The patient says their skin reddens with sun exposure; imaged for a research study, with no referral diagnosis recorded; the patient describes having few moles overall:
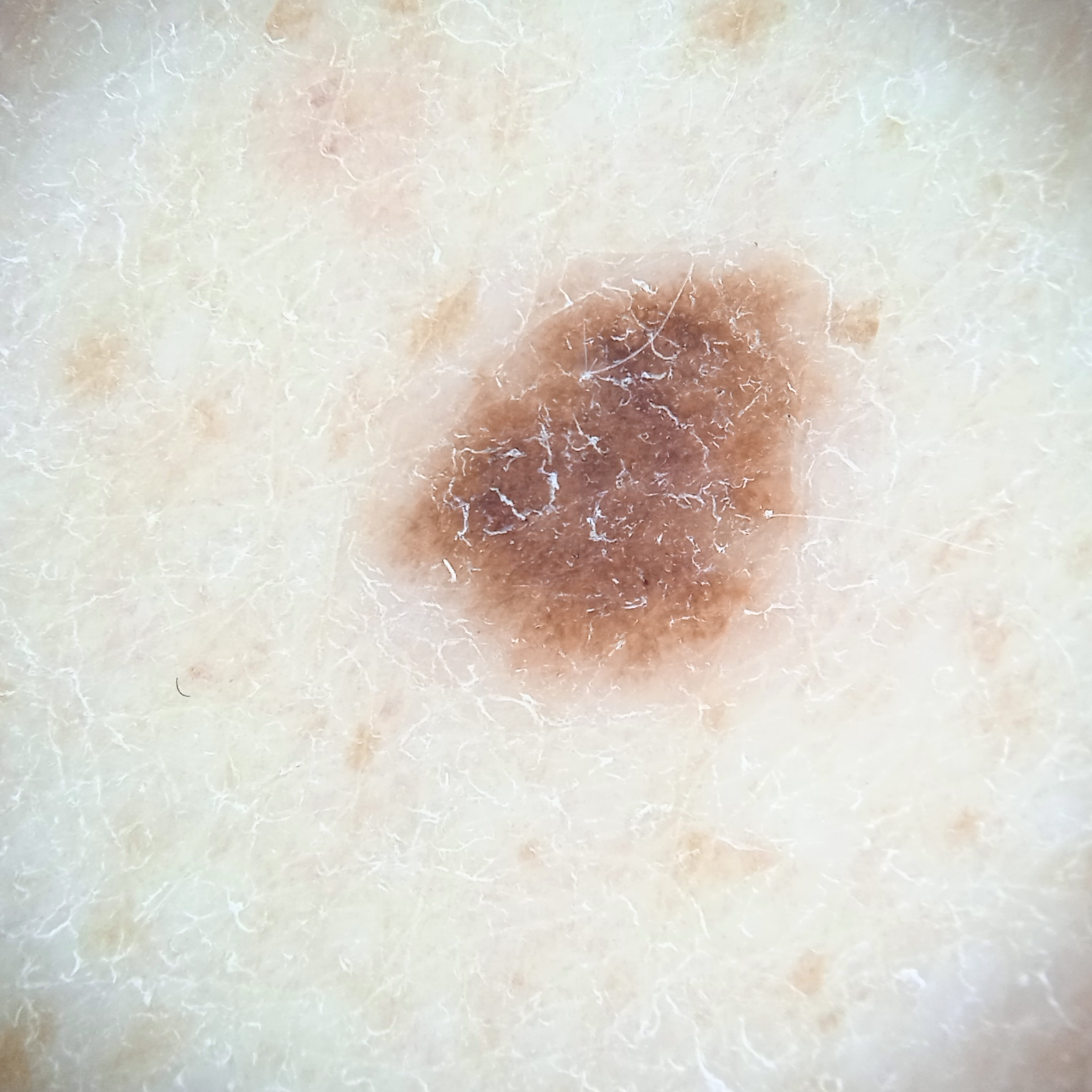Q: What is the anatomic site?
A: the back
Q: What was the diagnosis?
A: melanocytic nevus (dermatologist consensus)